The affected area is the head or neck · the photograph was taken at an angle.
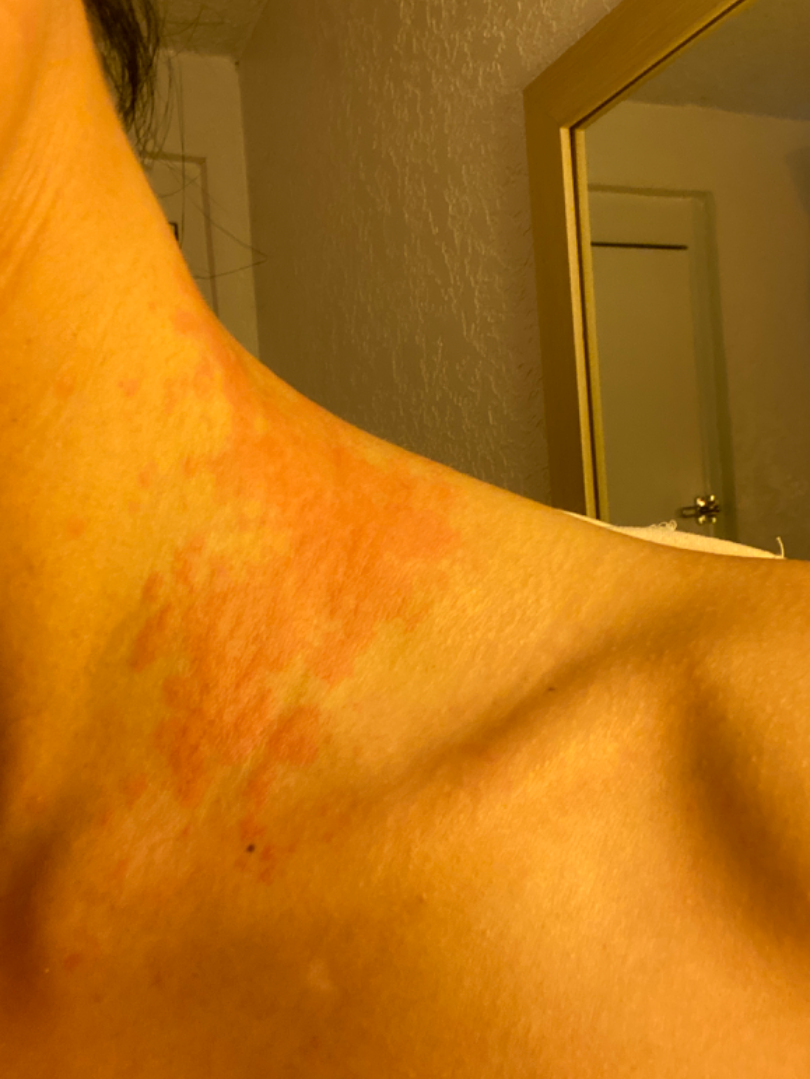Findings:
* assessment: ungradable on photographic review